A skin lesion imaged with a dermatoscope:
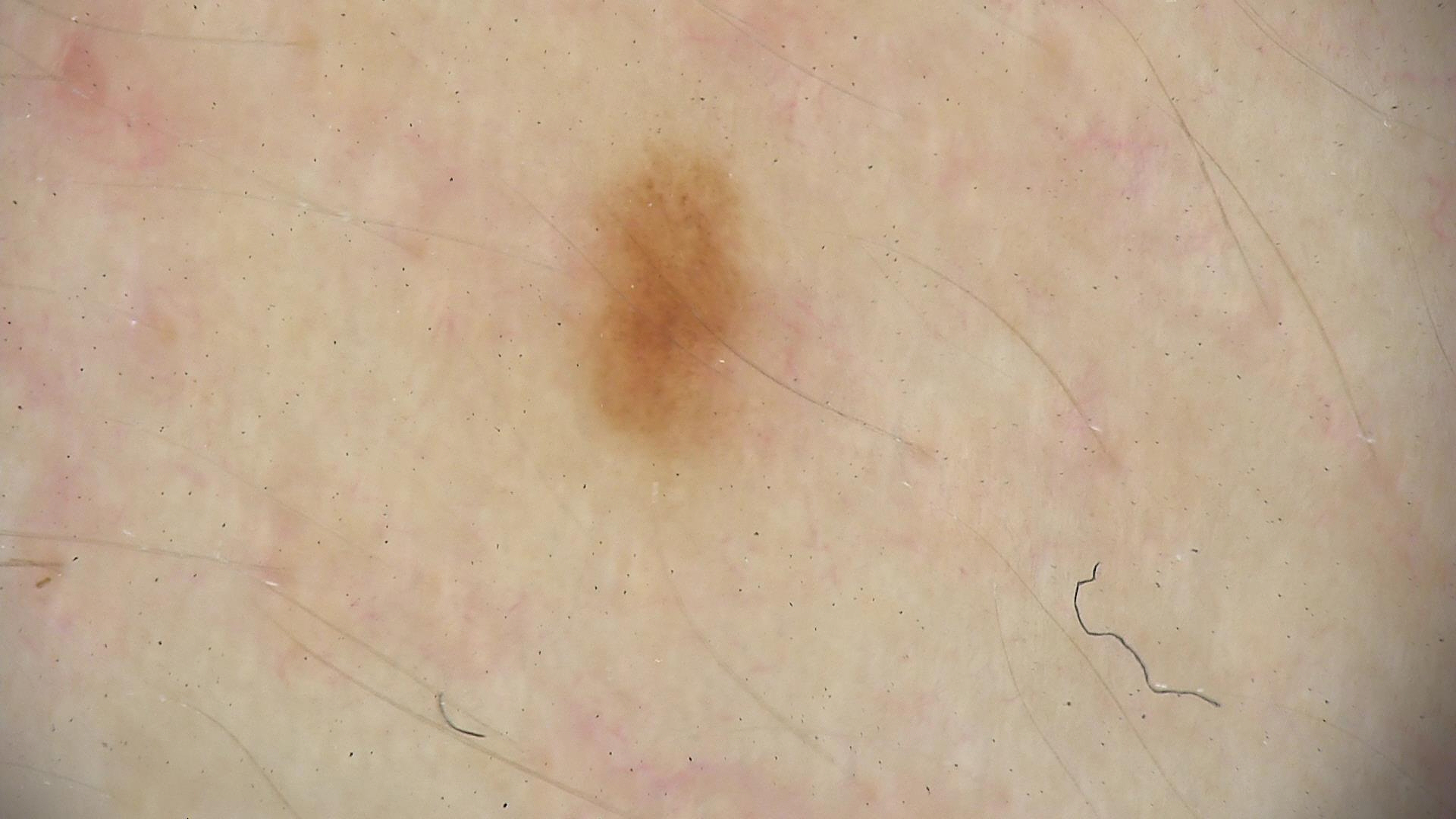{"diagnosis": {"name": "dysplastic junctional nevus", "code": "jd", "malignancy": "benign", "super_class": "melanocytic", "confirmation": "expert consensus"}}